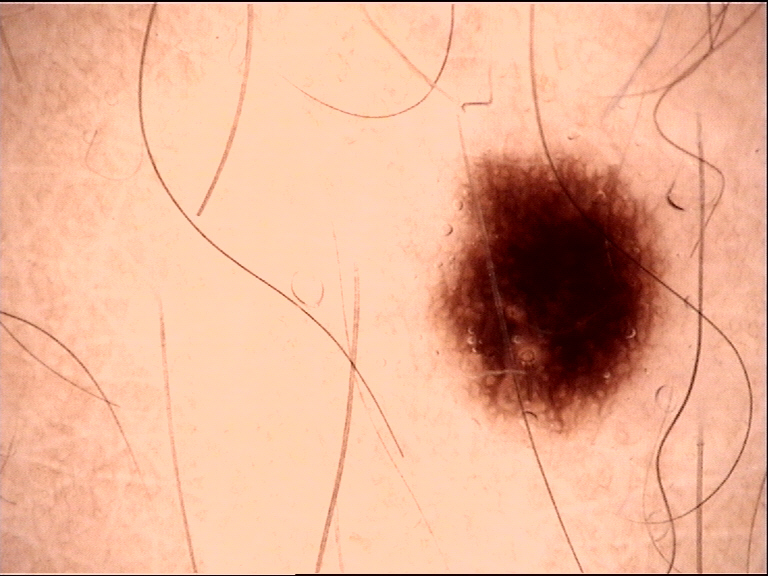image type — dermatoscopy
diagnostic label — dysplastic junctional nevus (expert consensus)